The patient is Fitzpatrick phototype II; a male subject in their mid- to late 60s; a clinical photograph showing a skin lesion in context — 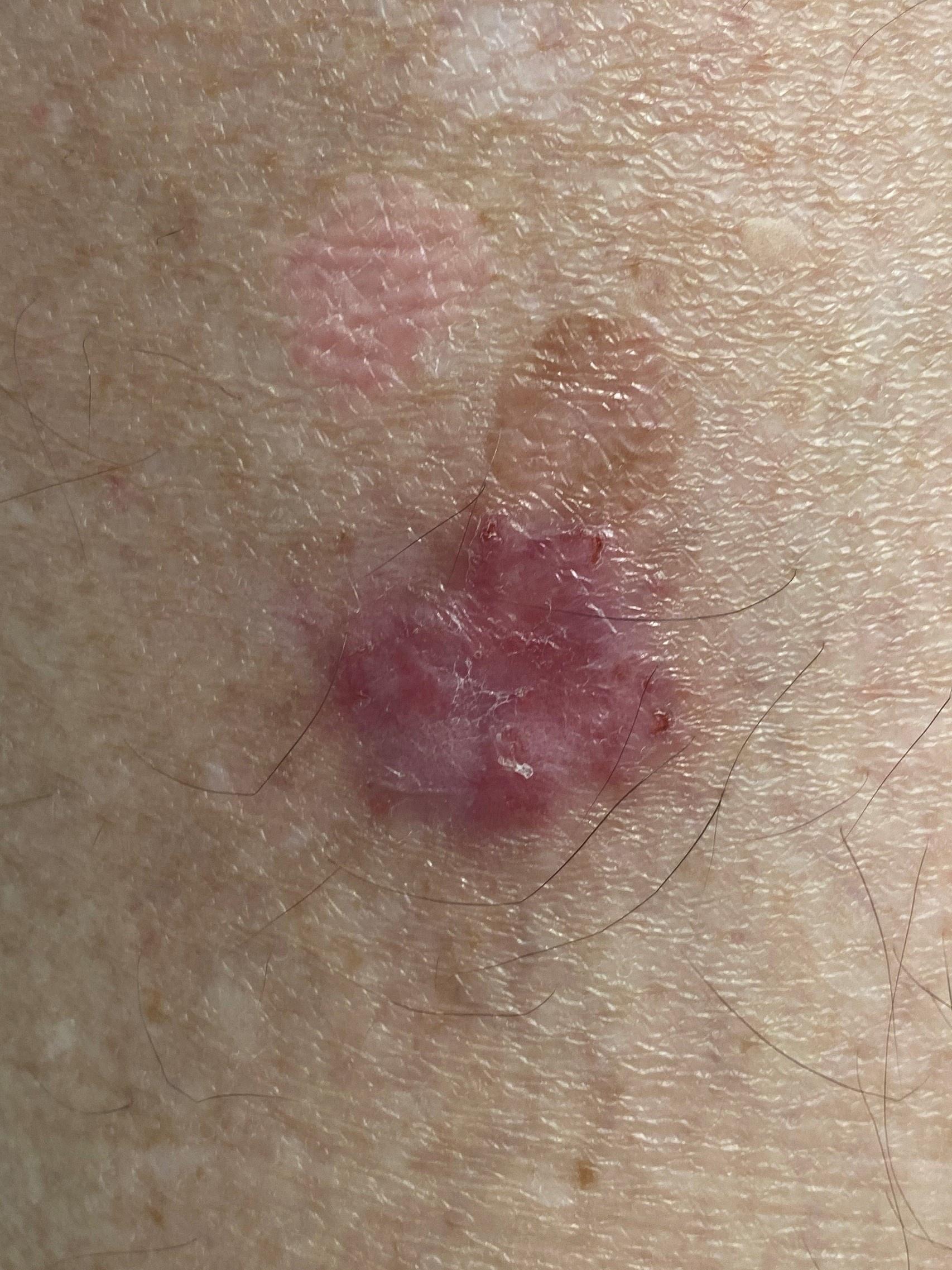The lesion was found on a lower extremity.
On biopsy, the diagnosis was a tumor of follicular differentiation — a basal cell carcinoma.